A dermoscopy image of a single skin lesion.
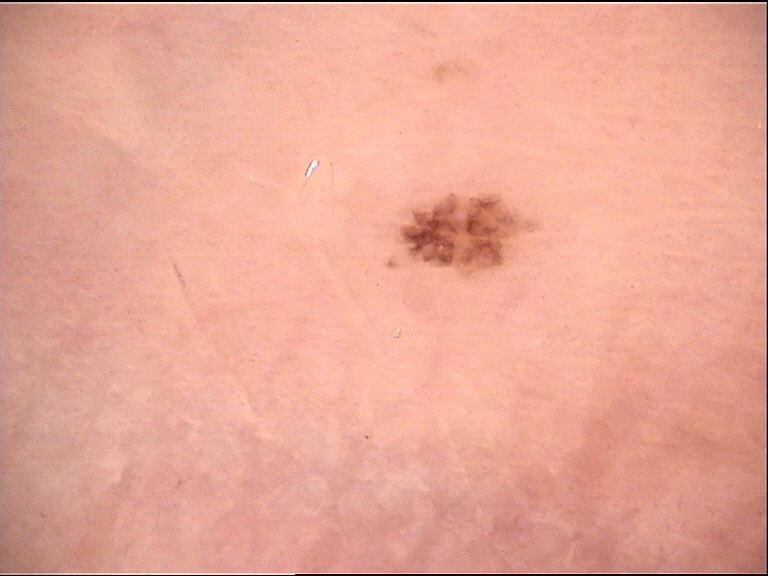| feature | finding |
|---|---|
| subtype | banal |
| class | junctional nevus (expert consensus) |